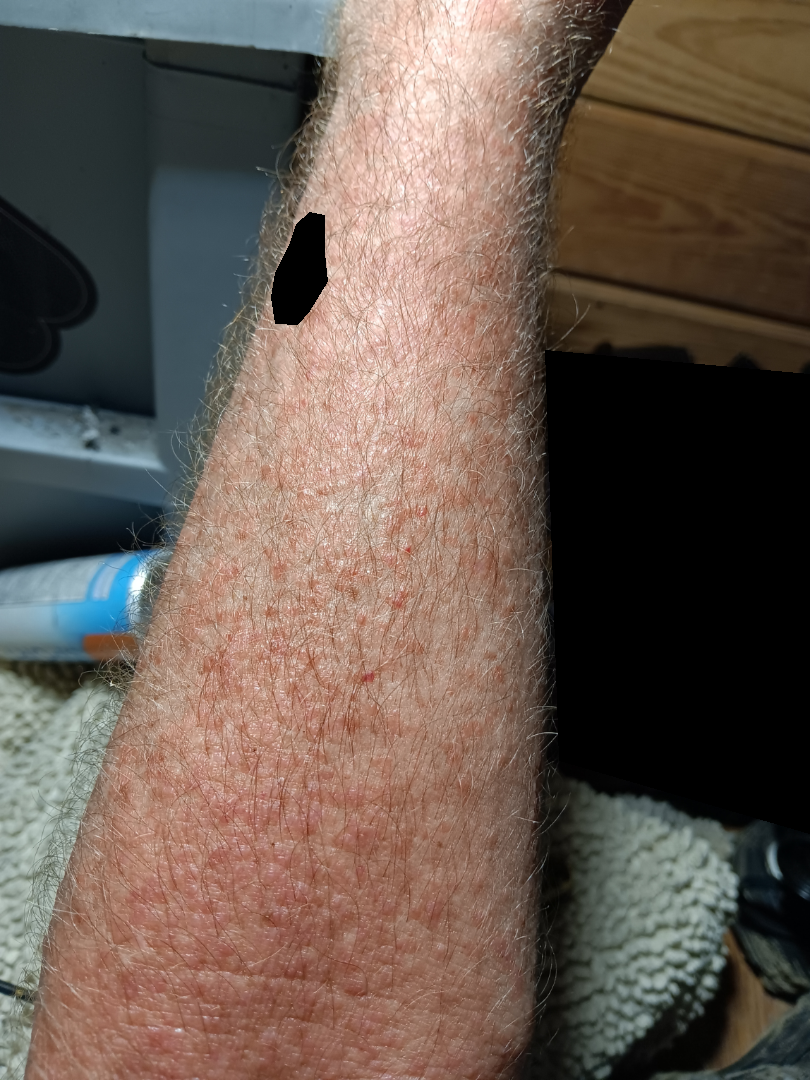  assessment: ungradable on photographic review